The affected area is the head or neck; close-up view: 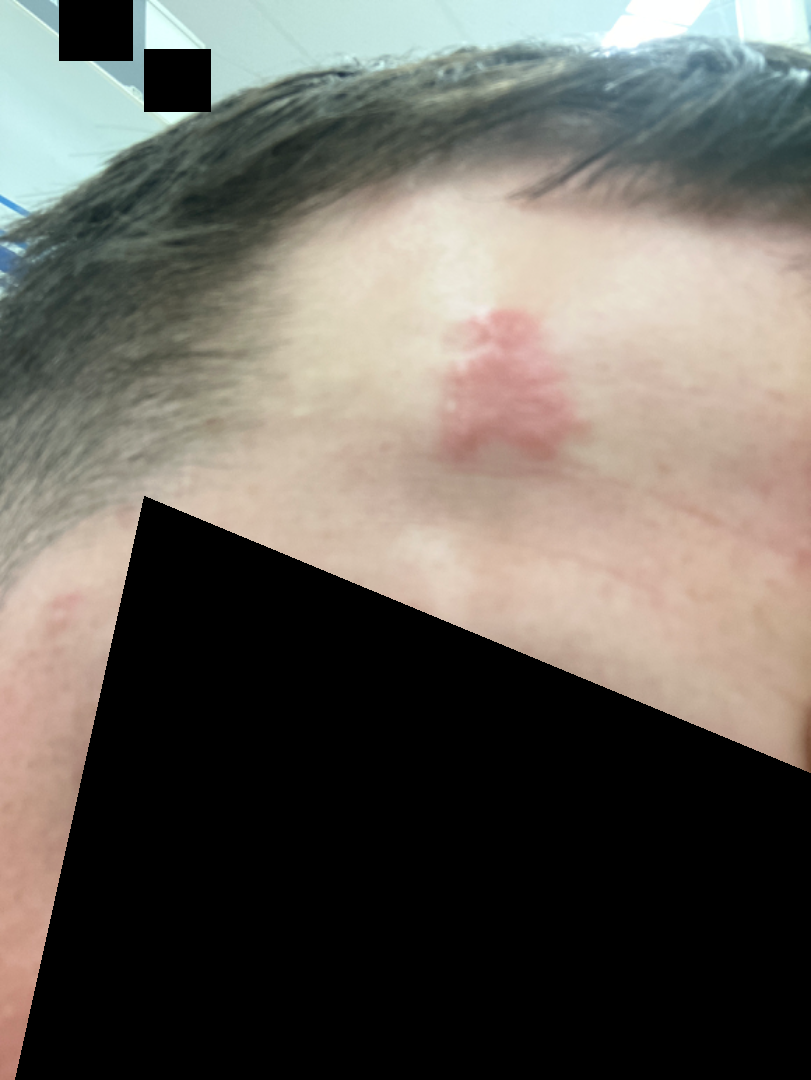The reviewer was unable to grade this case for skin condition. Reported duration is less than one week. FST II; lay graders estimated MST 2 or 3.